A close-up photograph:
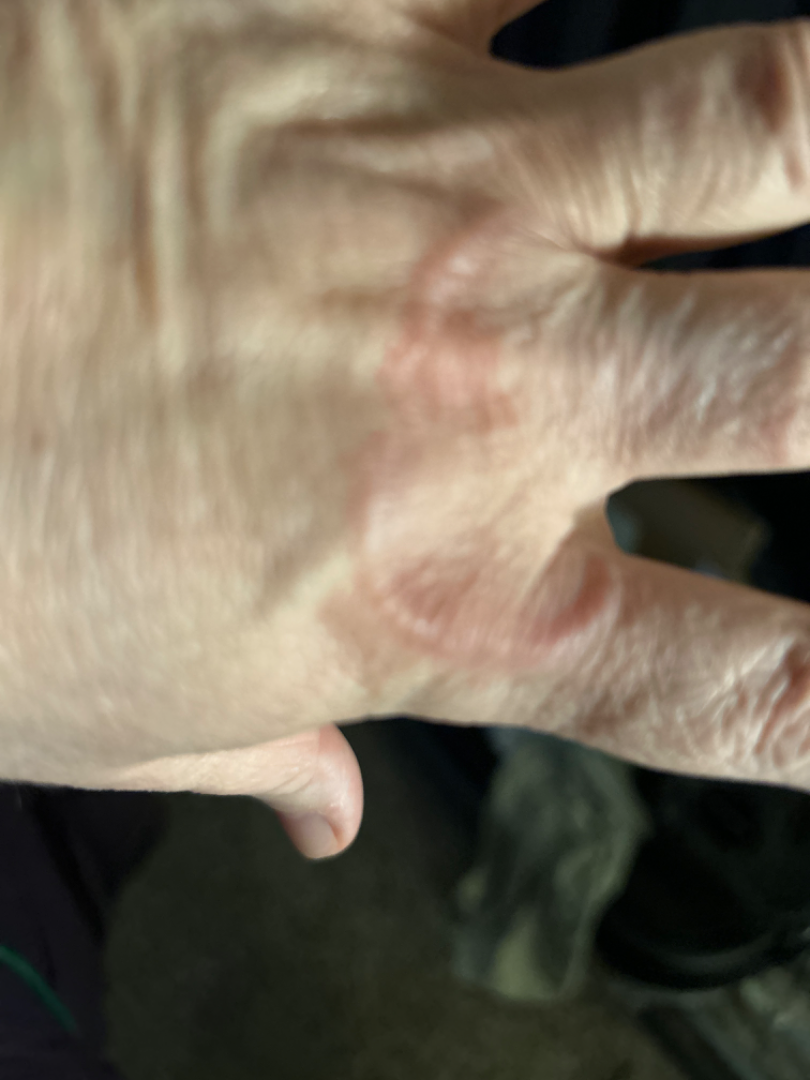Q: What is the differential diagnosis?
A: consistent with Granuloma annulare